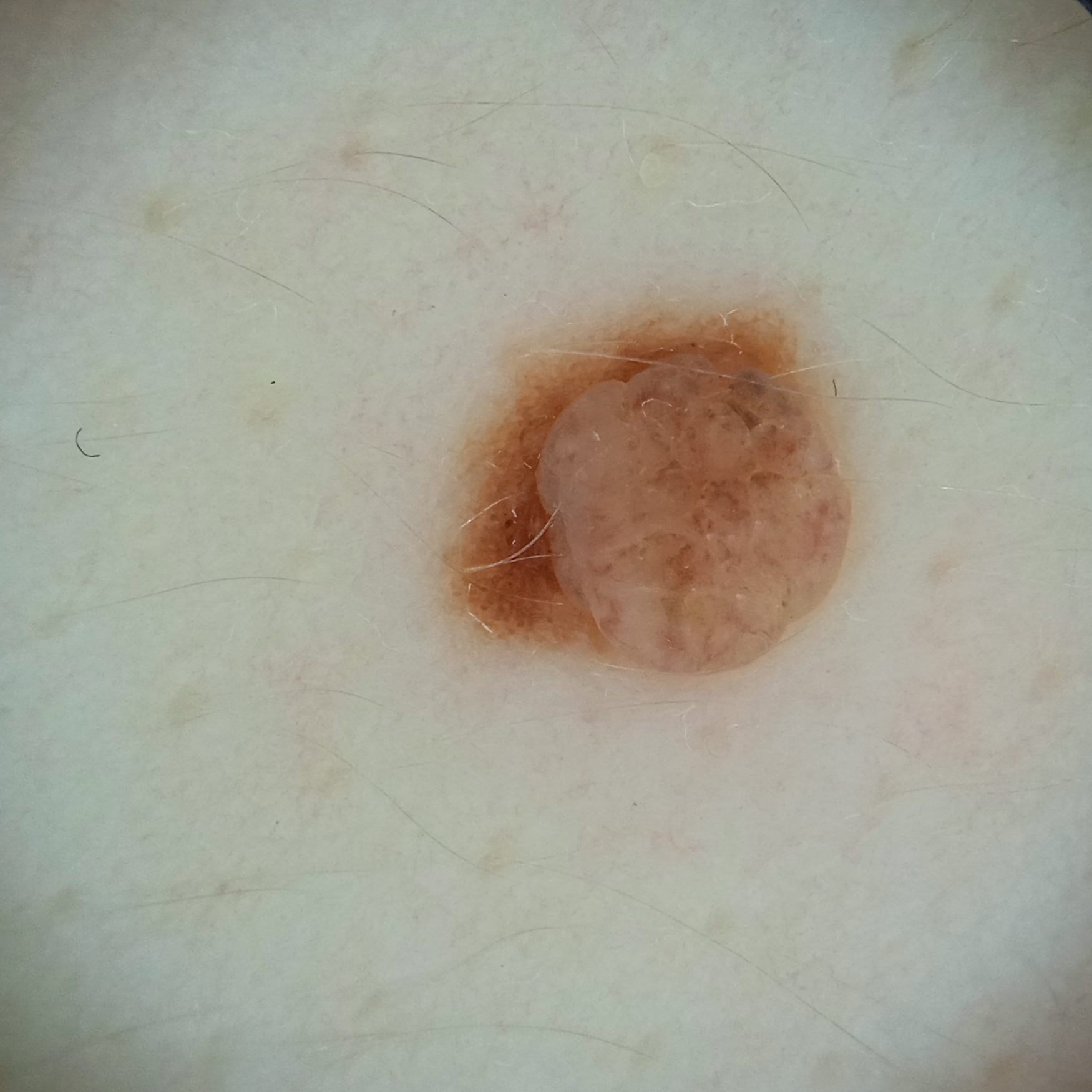<case>
  <sun_reaction>skin reddens with sun exposure</sun_reaction>
  <mole_burden>numerous melanocytic nevi</mole_burden>
  <patient>
    <age>26</age>
    <sex>female</sex>
  </patient>
  <risk_factors>
    <positive>a history of sunbed use</positive>
  </risk_factors>
  <referral>research study (no referral diagnosis)</referral>
  <lesion_location>the back</lesion_location>
  <diagnosis>
    <name>melanocytic nevus</name>
    <malignancy>benign</malignancy>
  </diagnosis>
</case>